Skin tone: Fitzpatrick skin type V · no relevant systemic symptoms · the lesion is associated with pain, burning and itching · the condition has been present for one to four weeks · the top or side of the foot is involved · an image taken at an angle · texture is reported as raised or bumpy and rough or flaky:
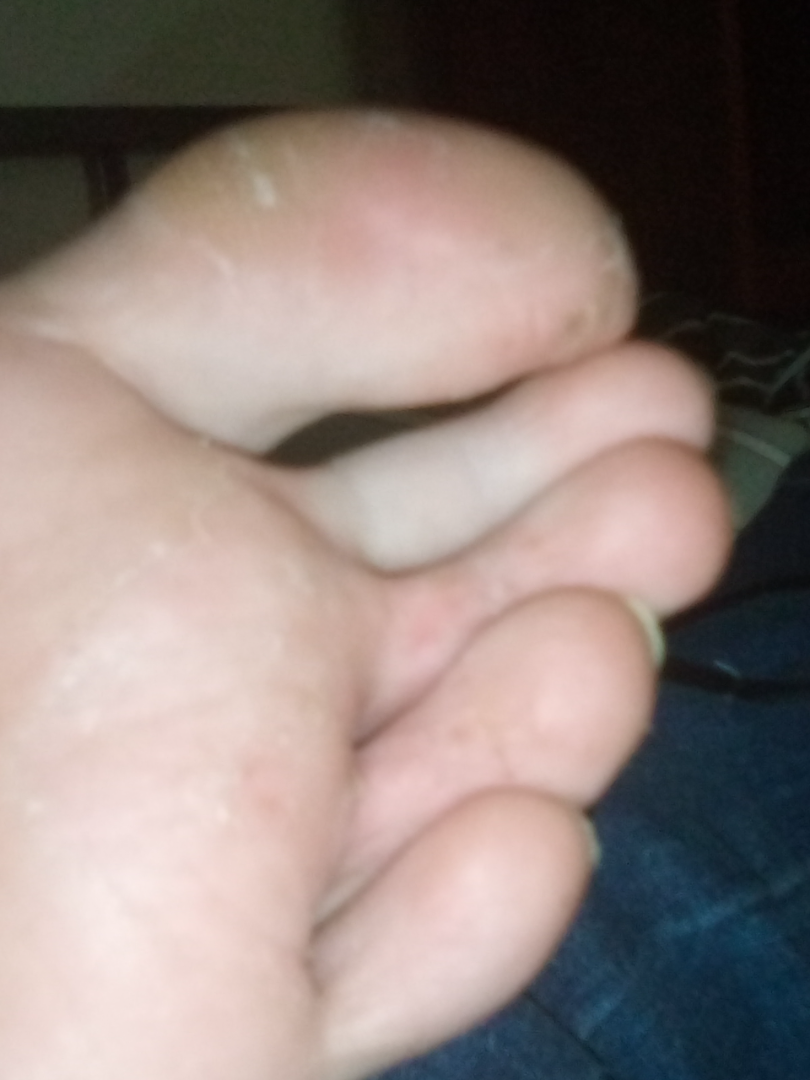Findings:
- dermatologist impression — most likely Tinea